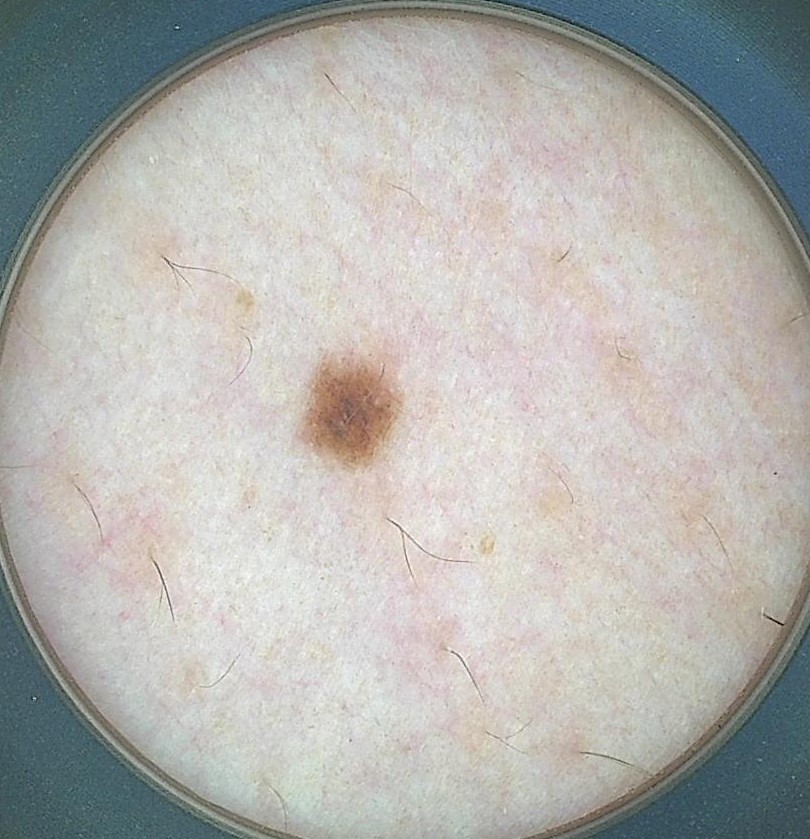diagnosis = dysplastic junctional nevus (expert consensus).